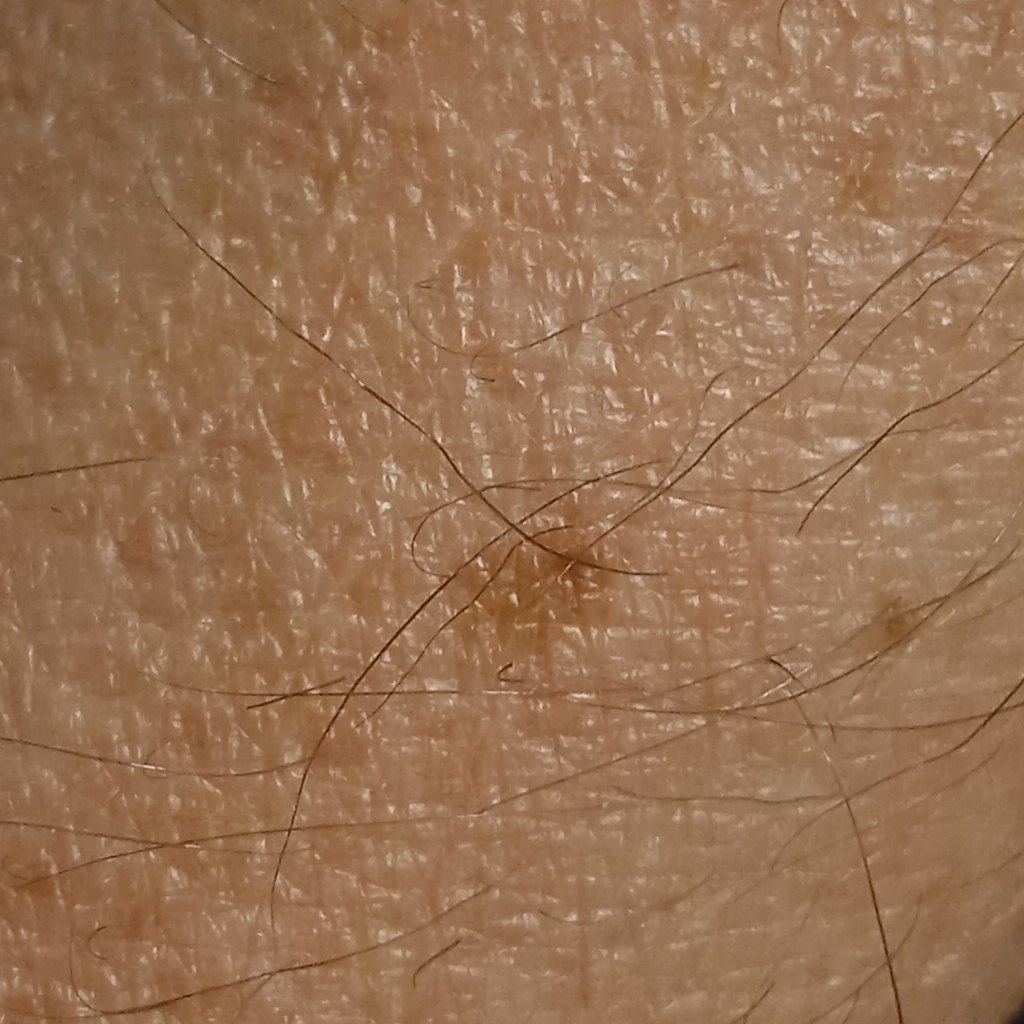patient=male, 79 years old | diagnostic label=seborrheic keratosis (dermatologist consensus).